The patient considered this a rash; close-up view; the contributor notes the condition has been present for less than one week; the lesion is associated with bothersome appearance; the contributor notes the lesion is rough or flaky; located on the leg.
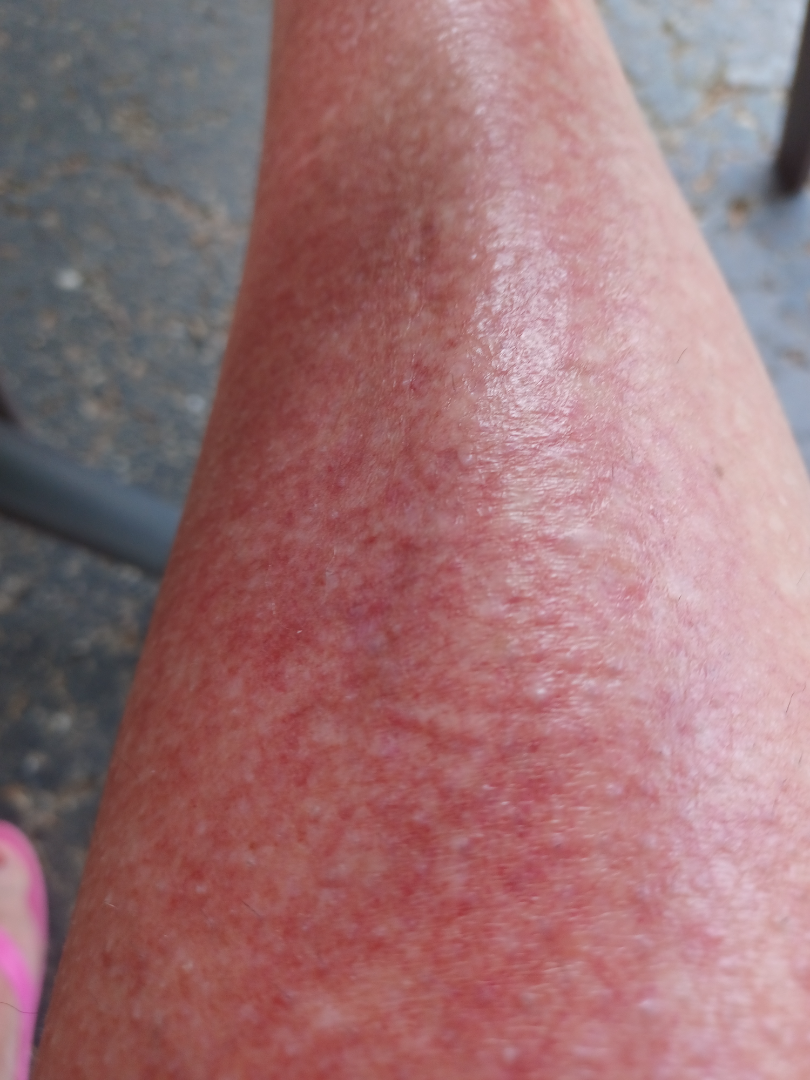| field | value |
|---|---|
| assessment | unable to determine |